A female patient in their 90s. The patient is skin type II. A clinical photo of a skin lesion taken with a smartphone:
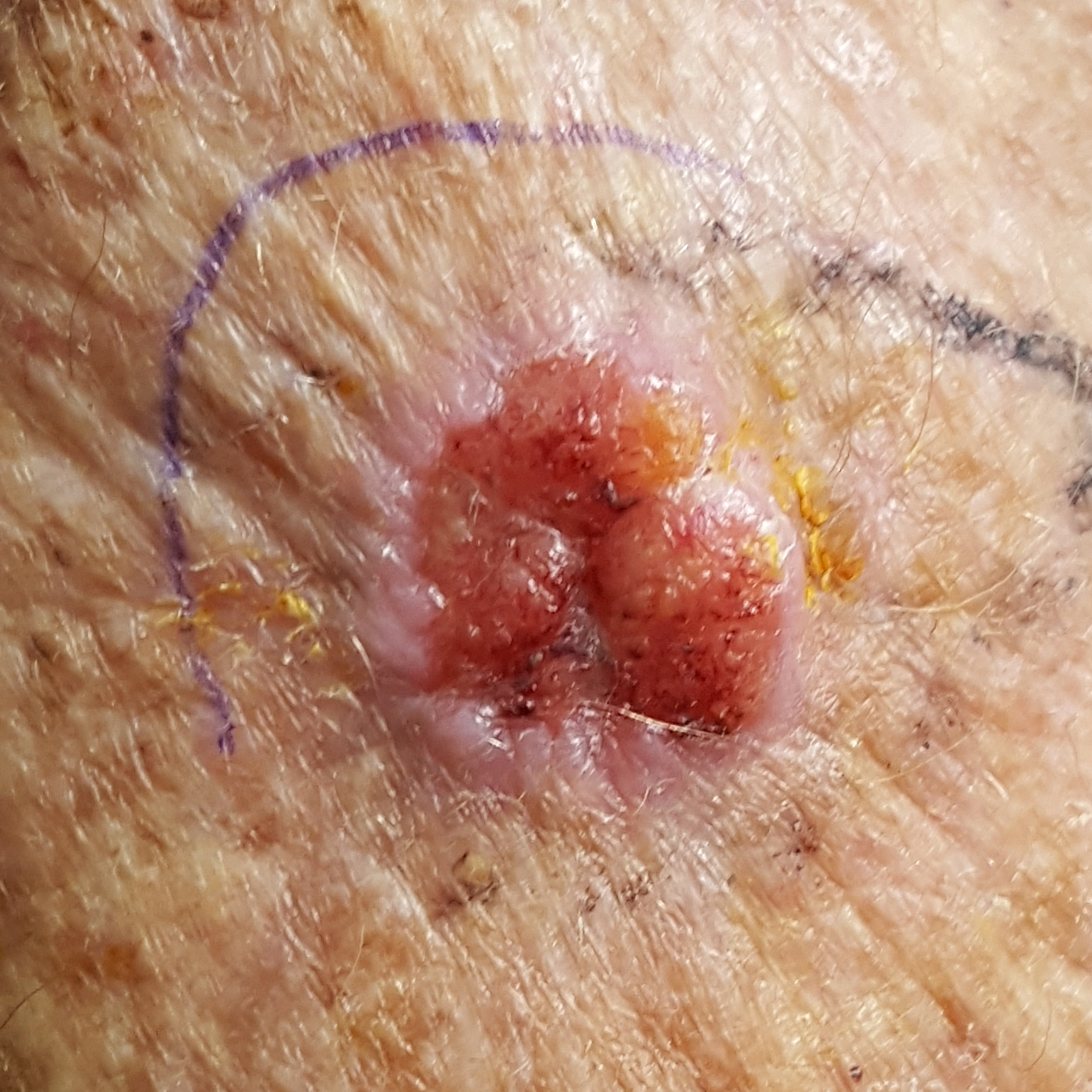Summary:
The lesion measures 17 × 15 mm. The patient reports that the lesion has bled, has grown, is elevated, itches, and hurts.
Conclusion:
Histopathologically confirmed as a malignancy — a squamous cell carcinoma.